A dermoscopy image of a single skin lesion.
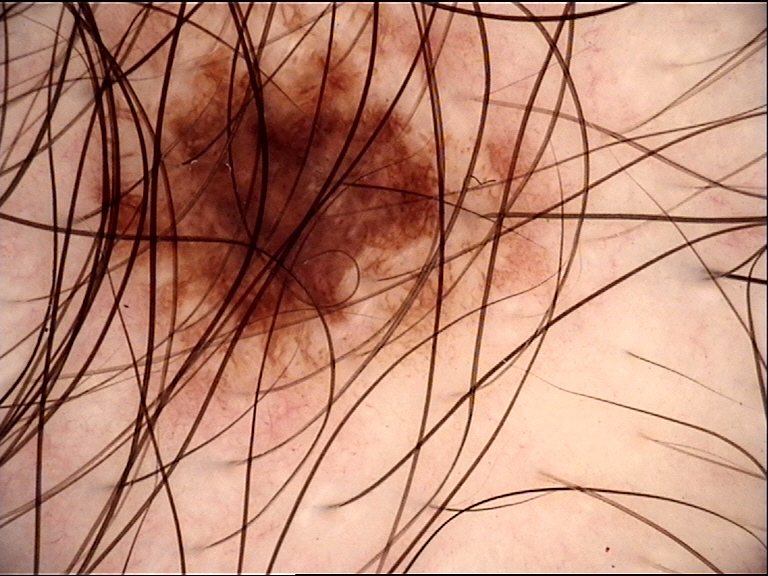Impression:
The diagnosis was a benign lesion — a dysplastic junctional nevus.